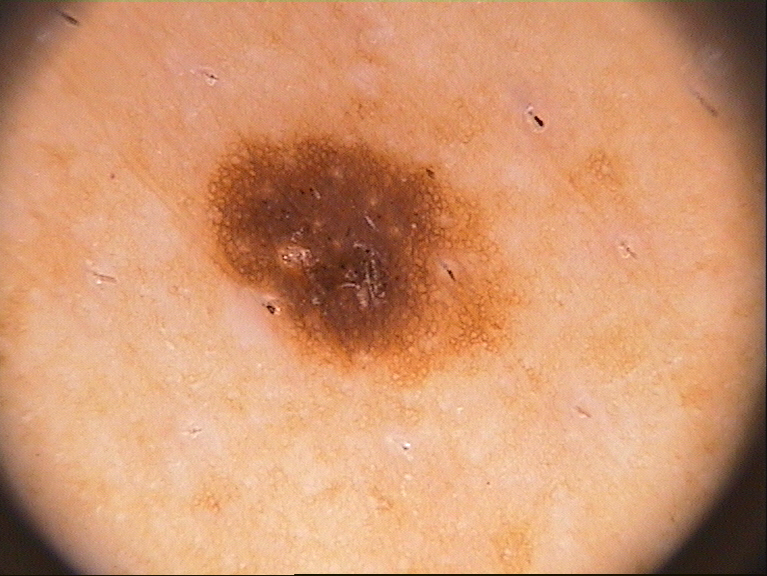imaging = dermoscopy of a skin lesion; patient = male, aged approximately 60; lesion bbox = left=198, top=97, right=540, bottom=399; features = pigment network and globules; extent = moderate; assessment = a melanocytic nevus, a benign skin lesion.